A dermoscopic view of a skin lesion — 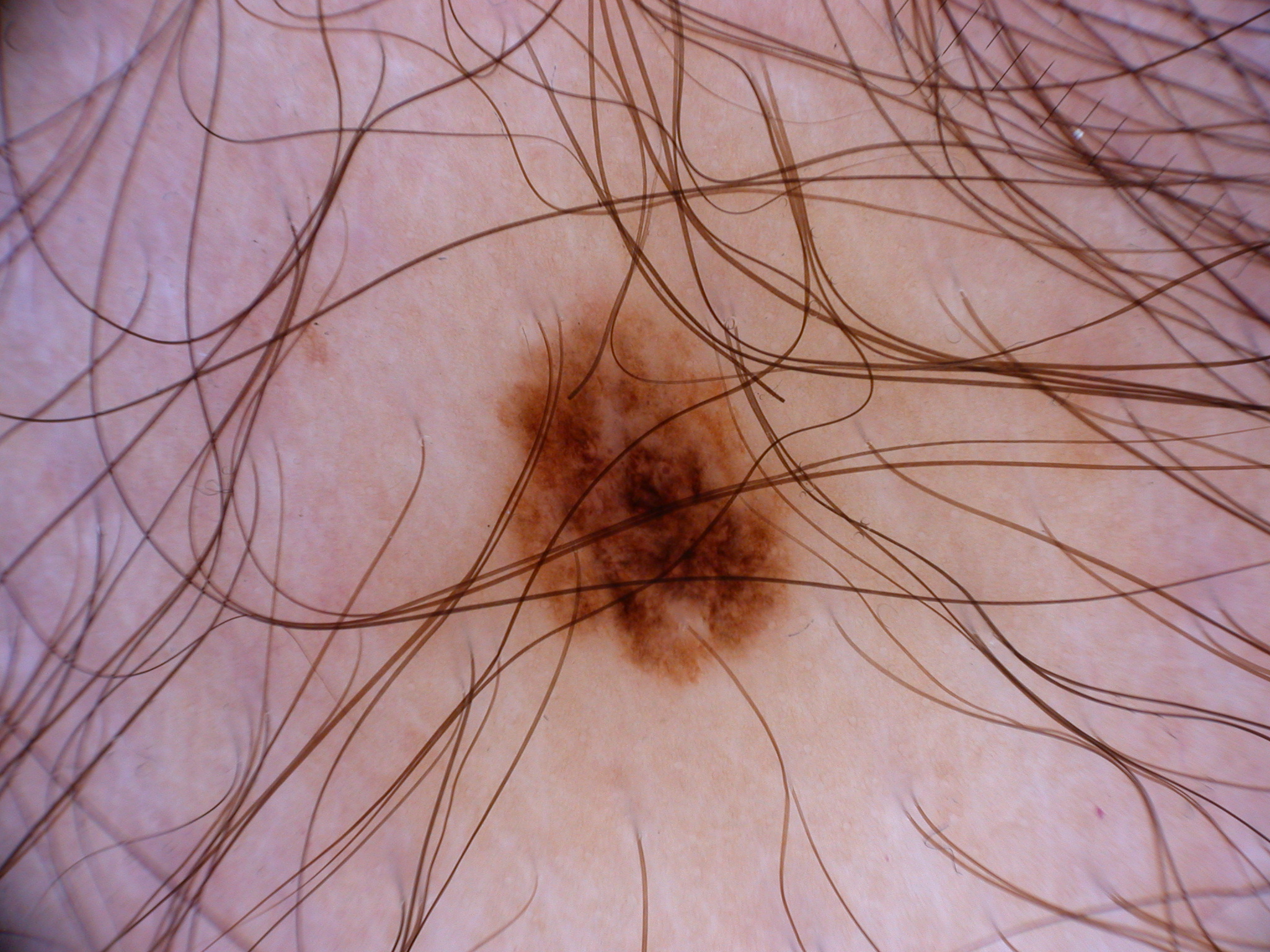Dermoscopically, the lesion shows globules and pigment network, with no milia-like cysts, negative network, or streaks. In (x1, y1, x2, y2) order, the lesion is bounded by <bbox>494, 287, 811, 697</bbox>. Diagnosed as a melanocytic nevus, a benign skin lesion.